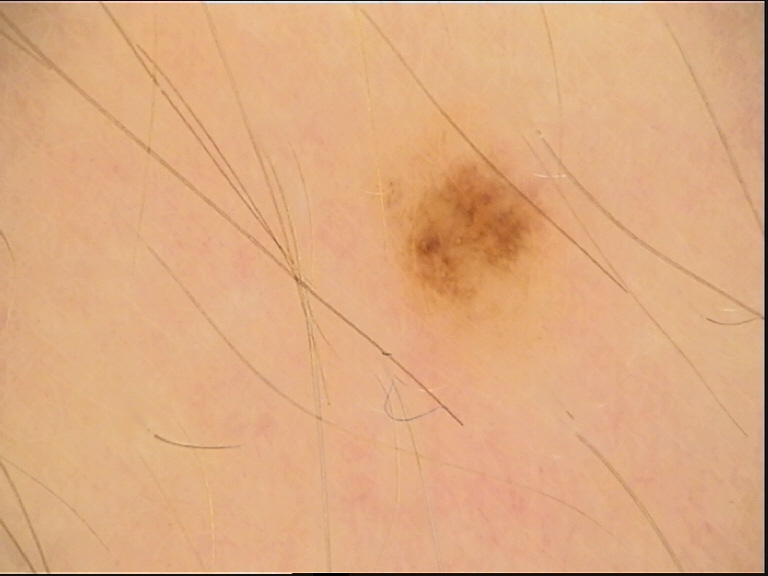Classified as a dysplastic junctional nevus.